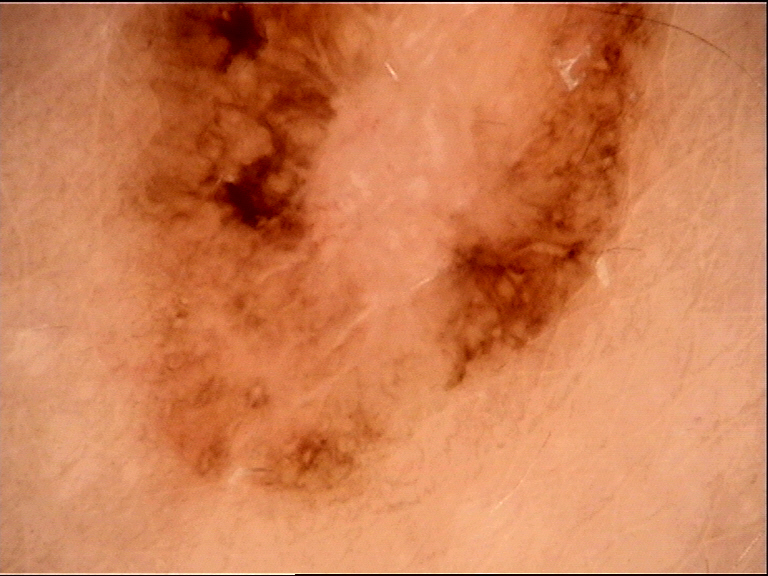A dermatoscopic image of a skin lesion. The biopsy diagnosis was a malignant lesion — a melanoma.